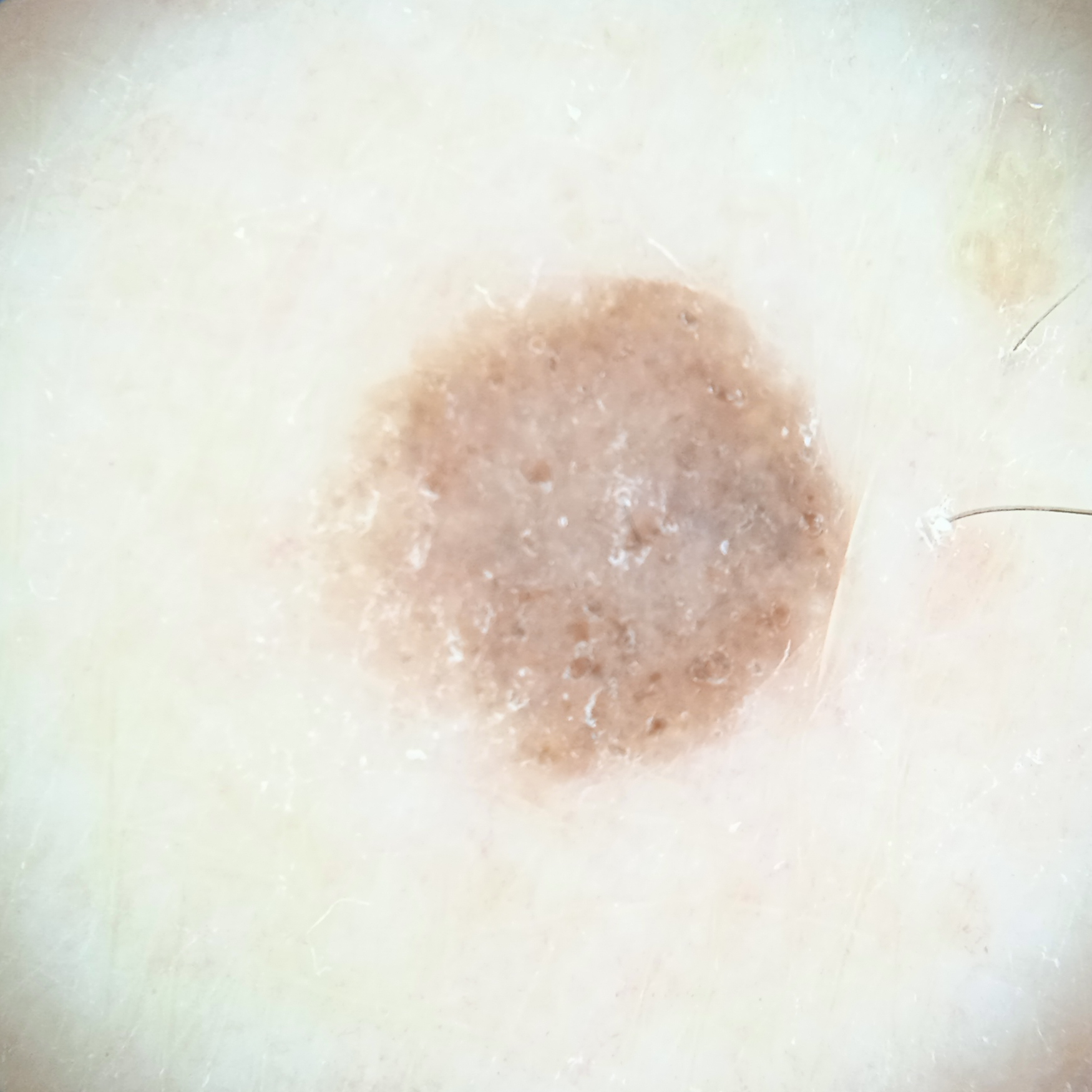<lesion>
<patient>
<age>79</age>
<sex>male</sex>
</patient>
<sun_reaction>skin tans without first burning</sun_reaction>
<mole_burden>few melanocytic nevi overall</mole_burden>
<image>dermoscopic image</image>
<referral>research study (no referral diagnosis)</referral>
<lesion_size>
<diameter_mm>5.8</diameter_mm>
</lesion_size>
<diagnosis>
<name>melanocytic nevus</name>
<malignancy>benign</malignancy>
</diagnosis>
</lesion>